The lesion involves the front of the torso, leg and arm · the patient is 18–29, male · a close-up photograph.
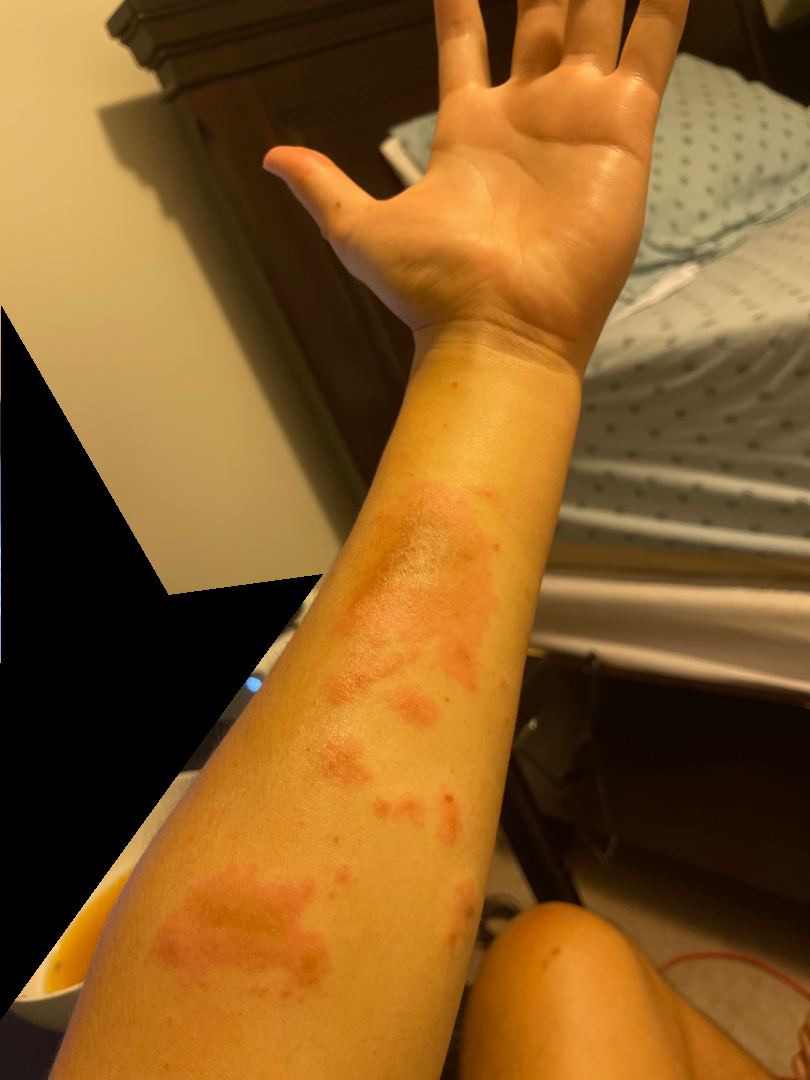differential = three independent reviewers: Contact dermatitis and Erythema multiforme were each considered, in no particular order; an alternative is Allergic Contact Dermatitis.